A dermoscopic view of a skin lesion.
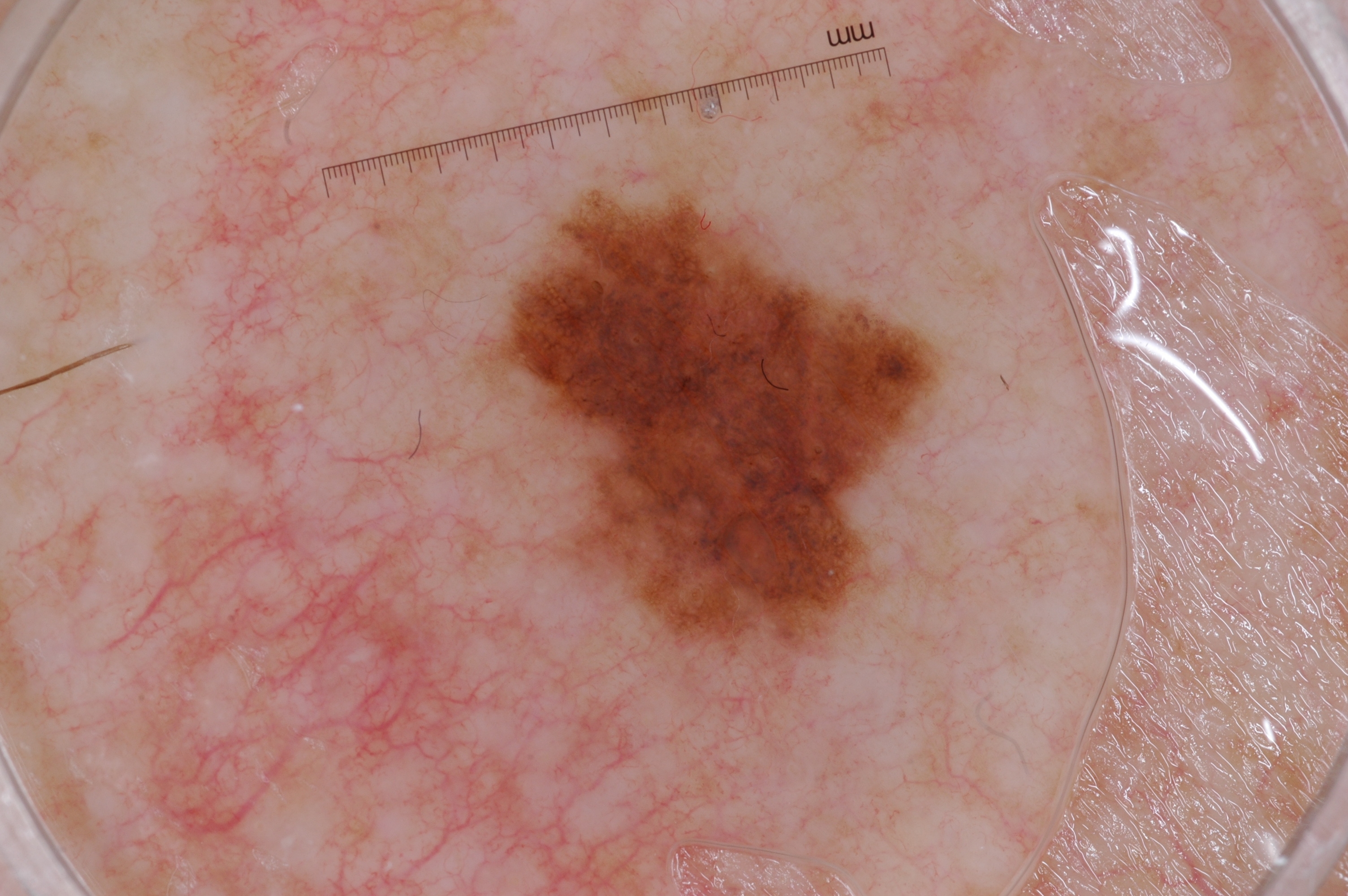<dermoscopy>
<dermoscopic_features>
  <present>milia-like cysts, pigment network</present>
  <absent>negative network, streaks</absent>
</dermoscopic_features>
<lesion_location>
  <bbox_xyxy>487, 190, 936, 657</bbox_xyxy>
</lesion_location>
<diagnosis>
  <name>melanoma</name>
  <malignancy>malignant</malignancy>
  <lineage>melanocytic</lineage>
  <provenance>histopathology</provenance>
</diagnosis>
</dermoscopy>